The arm, front of the torso and back of the hand are involved; female contributor, age 50–59; the photograph was taken at an angle — 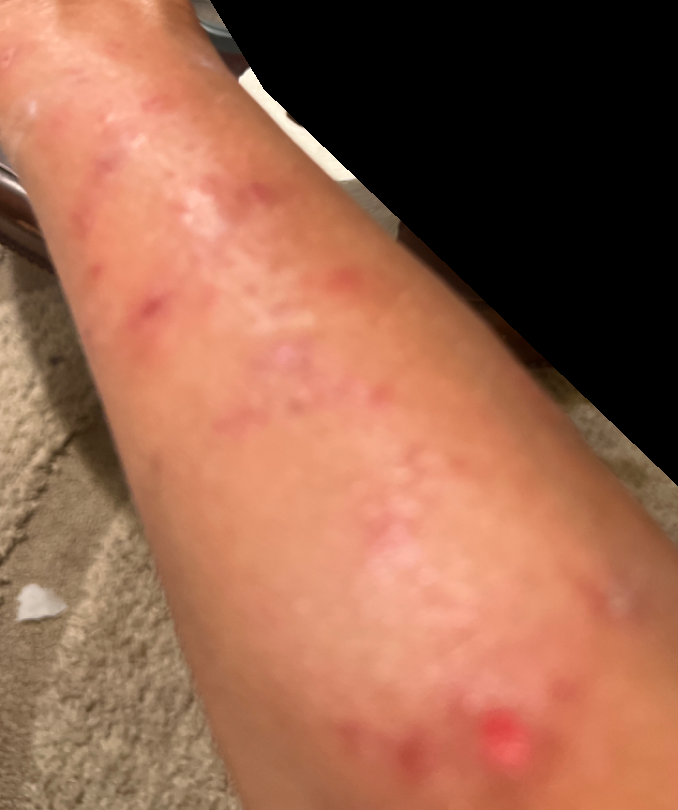Review:
On dermatologist assessment of the image, the differential, in no particular order, includes Prurigo nodularis and Abrasion, scrape, or scab; a more distant consideration is Insect Bite; less likely is Allergic Contact Dermatitis.